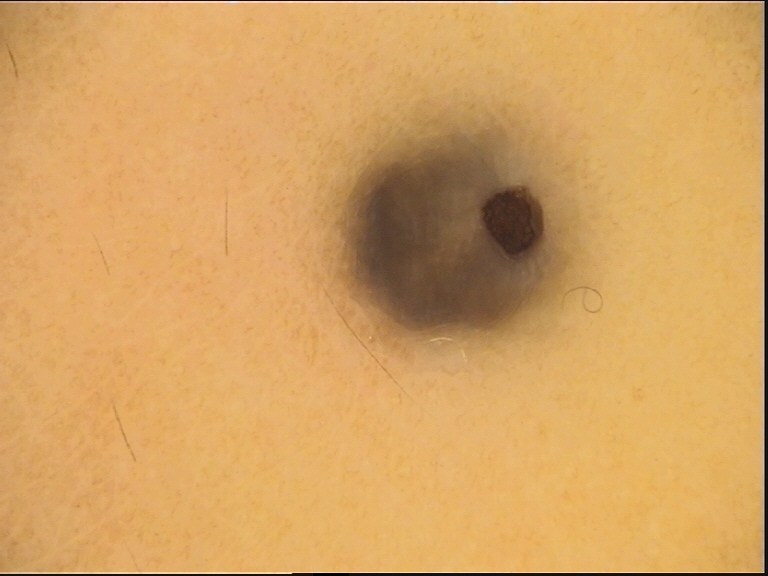A dermoscopic close-up of a skin lesion. The morphology is that of a dermal, banal lesion. Classified as a blue nevus.